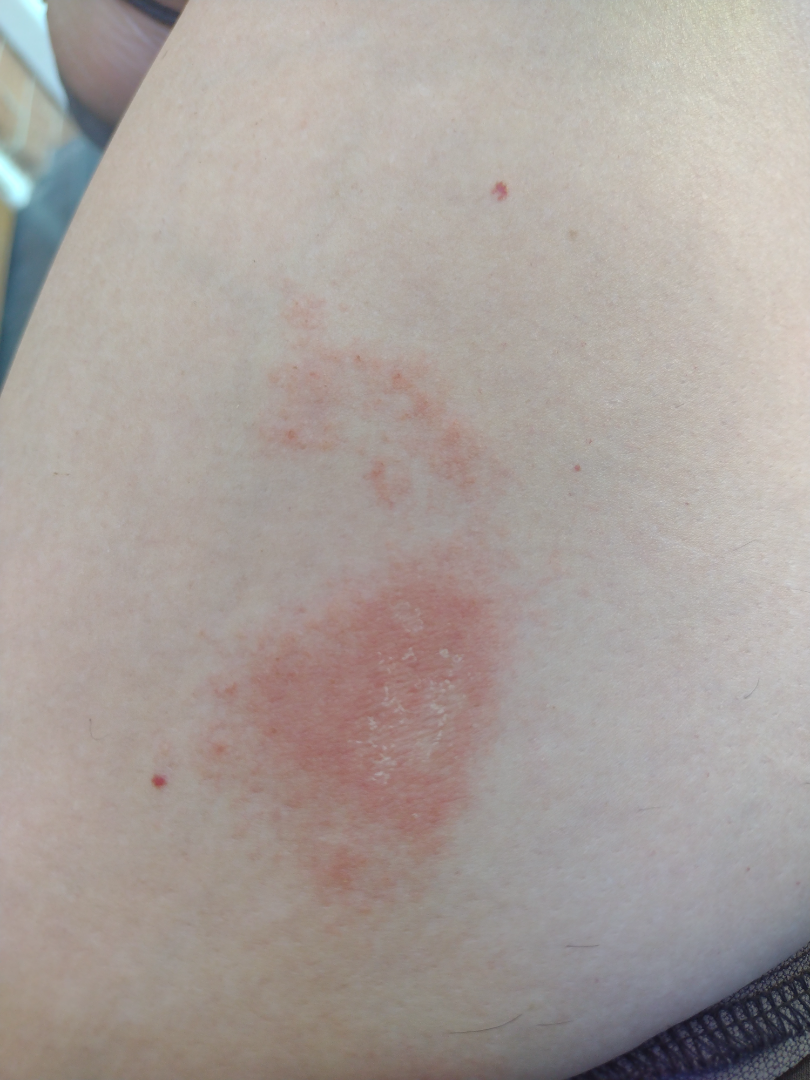Patient information:
The lesion is associated with bothersome appearance, enlargement and itching. Present for one to four weeks. The leg is involved. A close-up photograph.
Review:
On photographic review by a dermatologist, Irritant Contact Dermatitis (considered); Allergic Contact Dermatitis (considered); Eczema (lower probability).